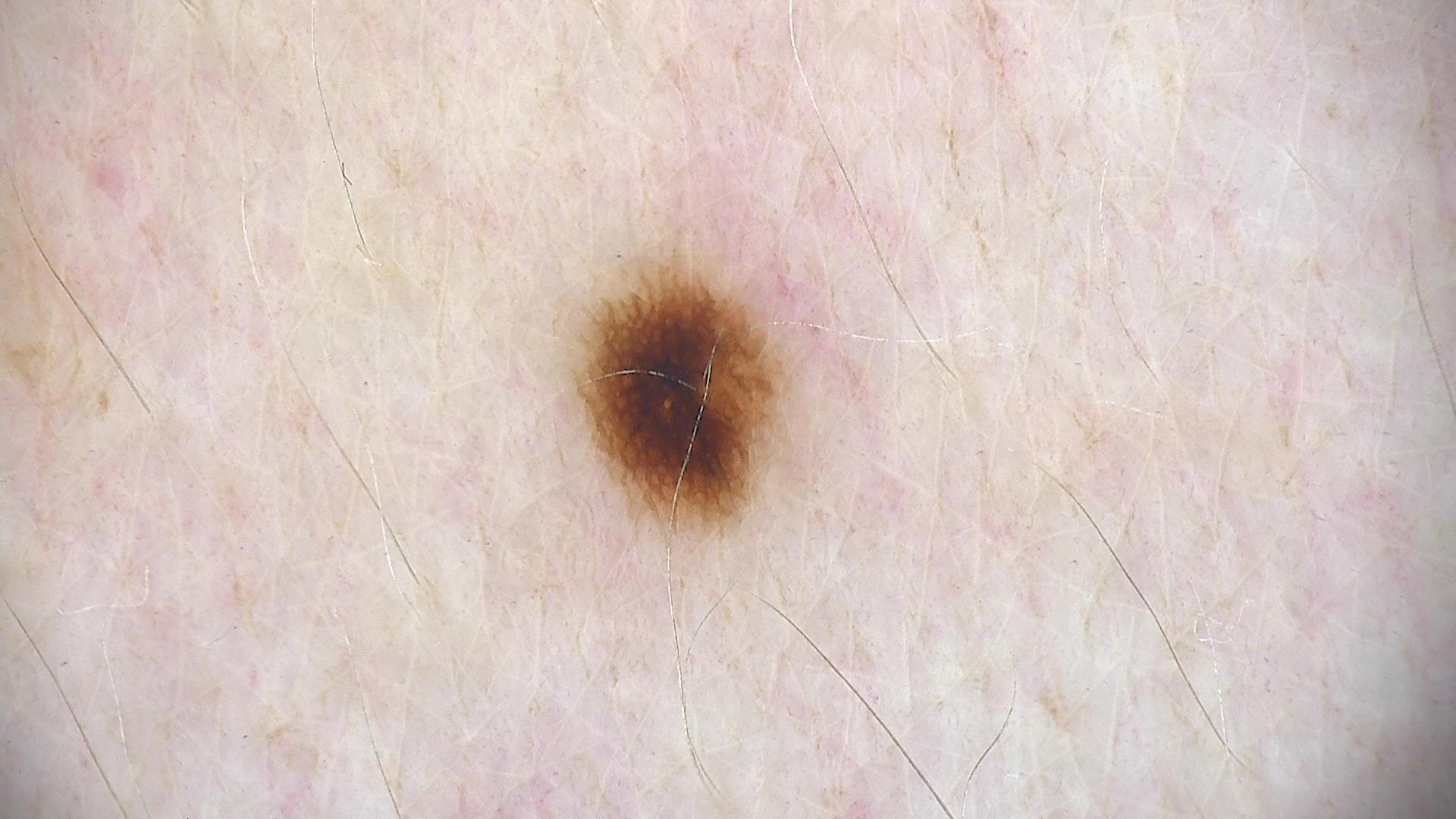| field | value |
|---|---|
| imaging | dermatoscopy |
| class | dysplastic junctional nevus (expert consensus) |